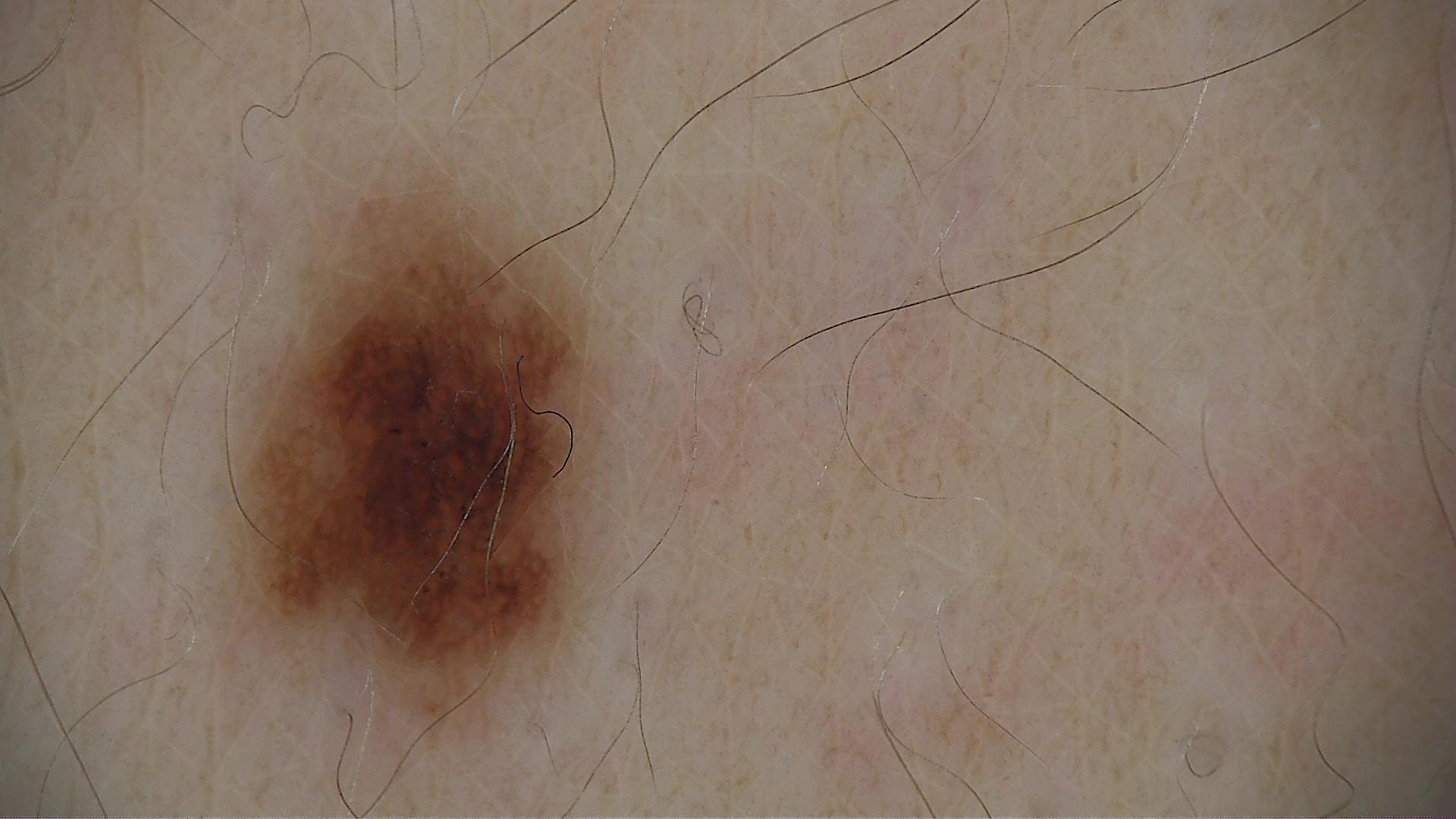Consistent with a dysplastic junctional nevus.